A male patient; a dermoscopic view of a skin lesion: 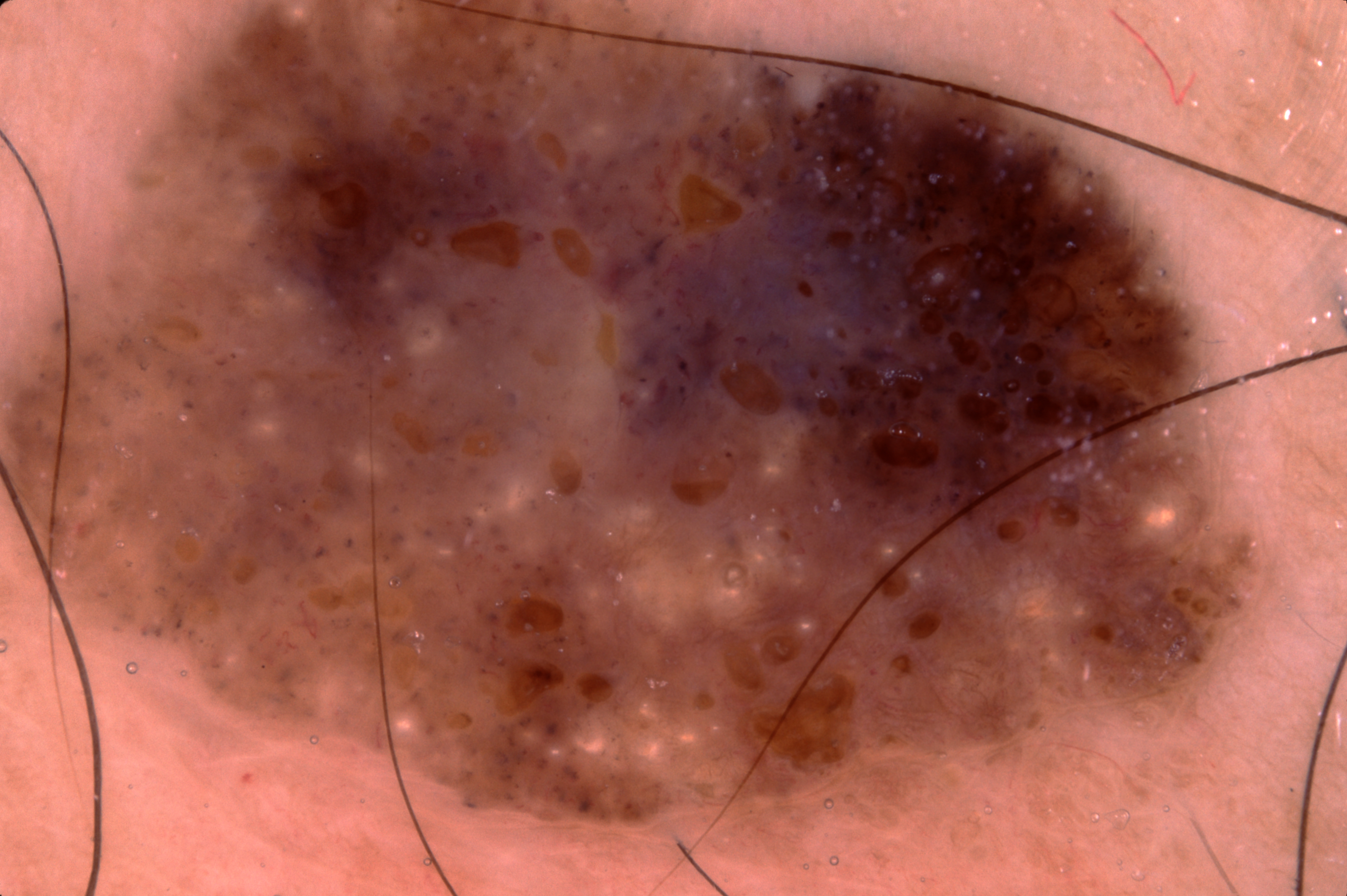Summary:
Dermoscopic review identifies milia-like cysts. The lesion stretches across essentially the whole frame.
Assessment:
Diagnosed as a seborrheic keratosis.